A clinical photograph of a skin lesion: 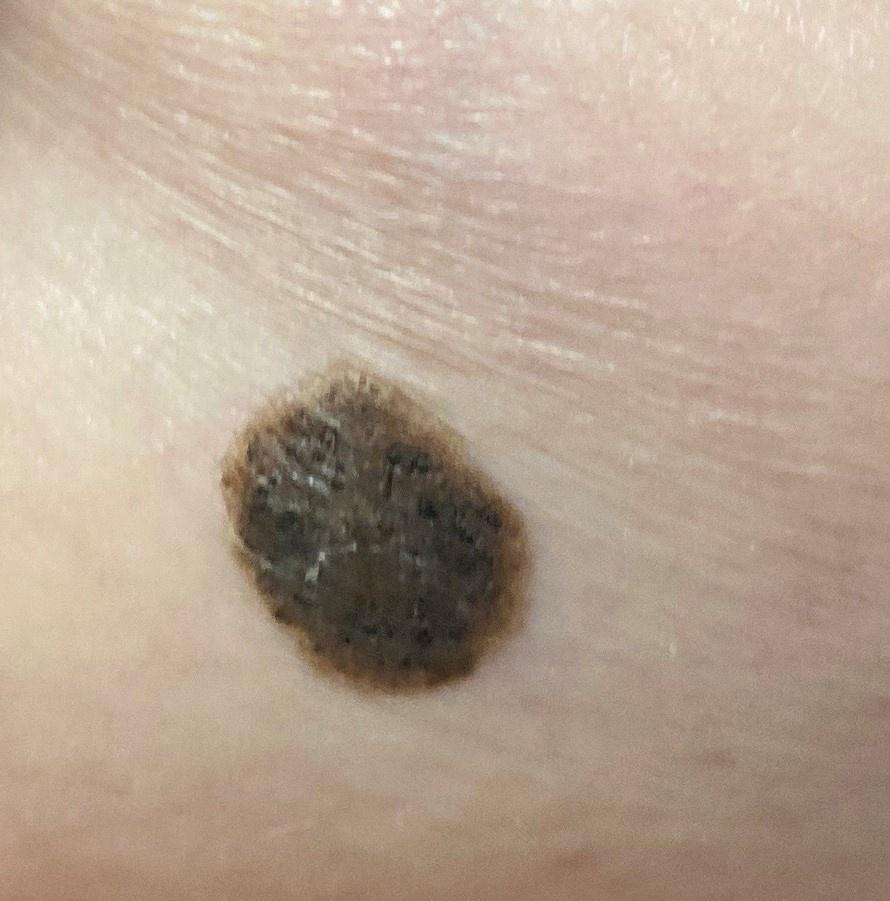The lesion is located on the anterior trunk. Consistent with a seborrheic keratosis.